Located on the leg, an image taken at a distance:
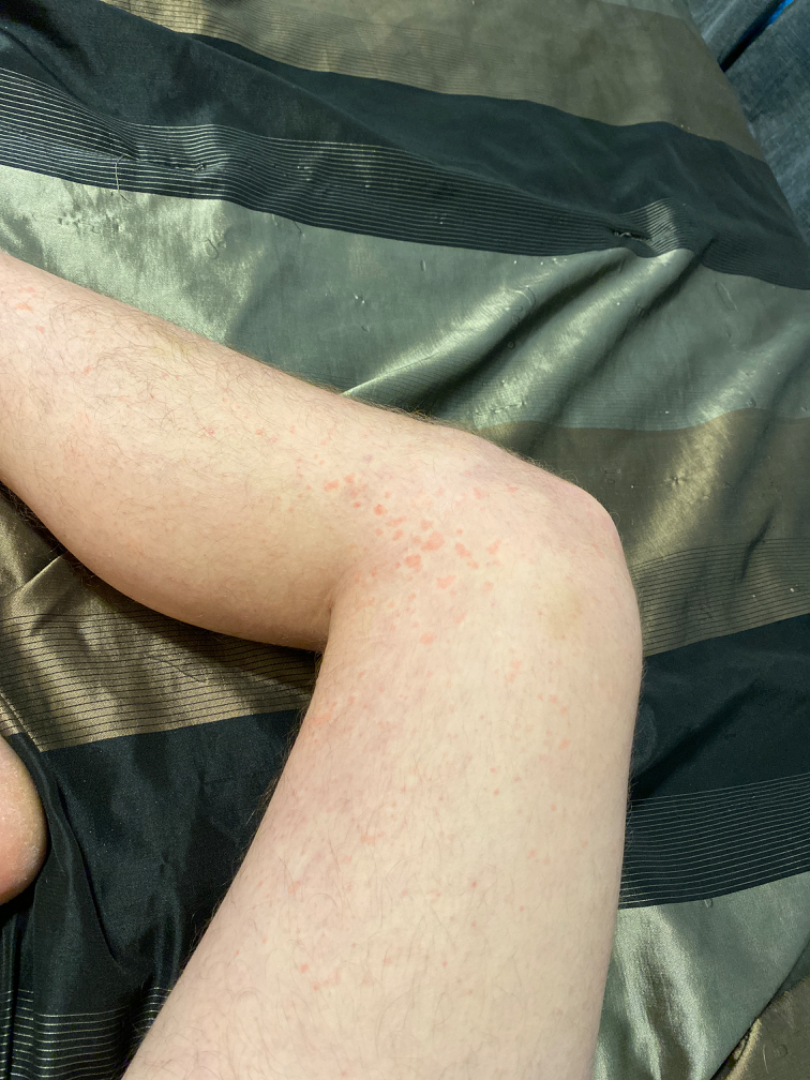Findings: Single-reviewer assessment: the primary impression is Urticaria; also consider Leukocytoclastic Vasculitis.